An image taken at a distance, located on the head or neck and arm, the patient is a female aged 18–29 — 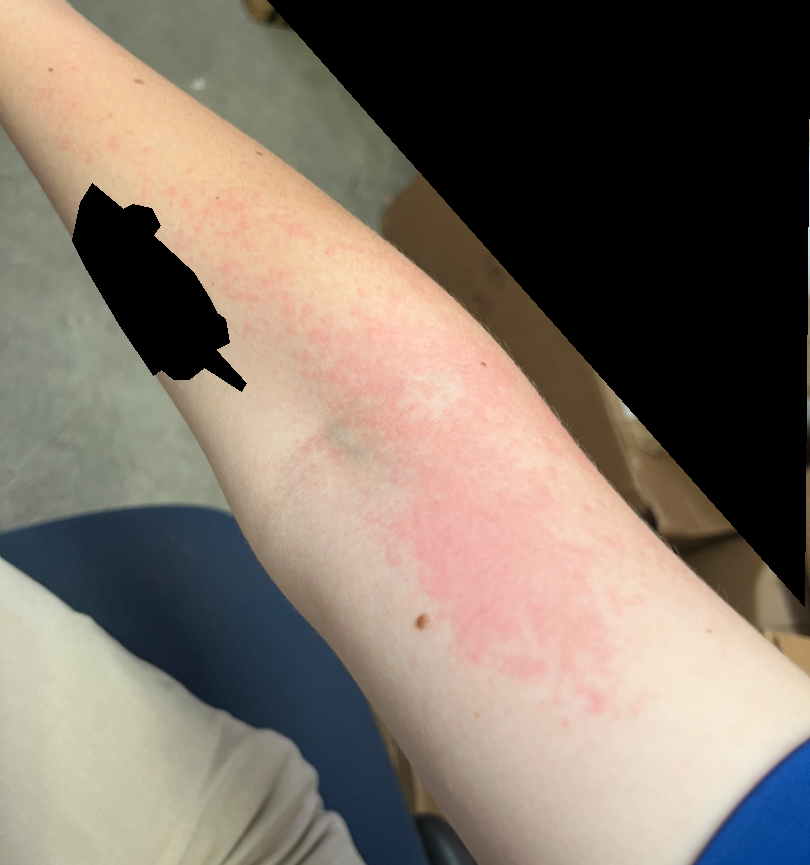constitutional symptoms — shortness of breath | texture — raised or bumpy | patient-reported symptoms — itching and burning | differential diagnosis — Acute dermatitis, NOS (leading).